The contributor reports bothersome appearance · male subject, age 70–79 · the top or side of the foot and leg are involved · the contributor reports the lesion is raised or bumpy · a close-up photograph:
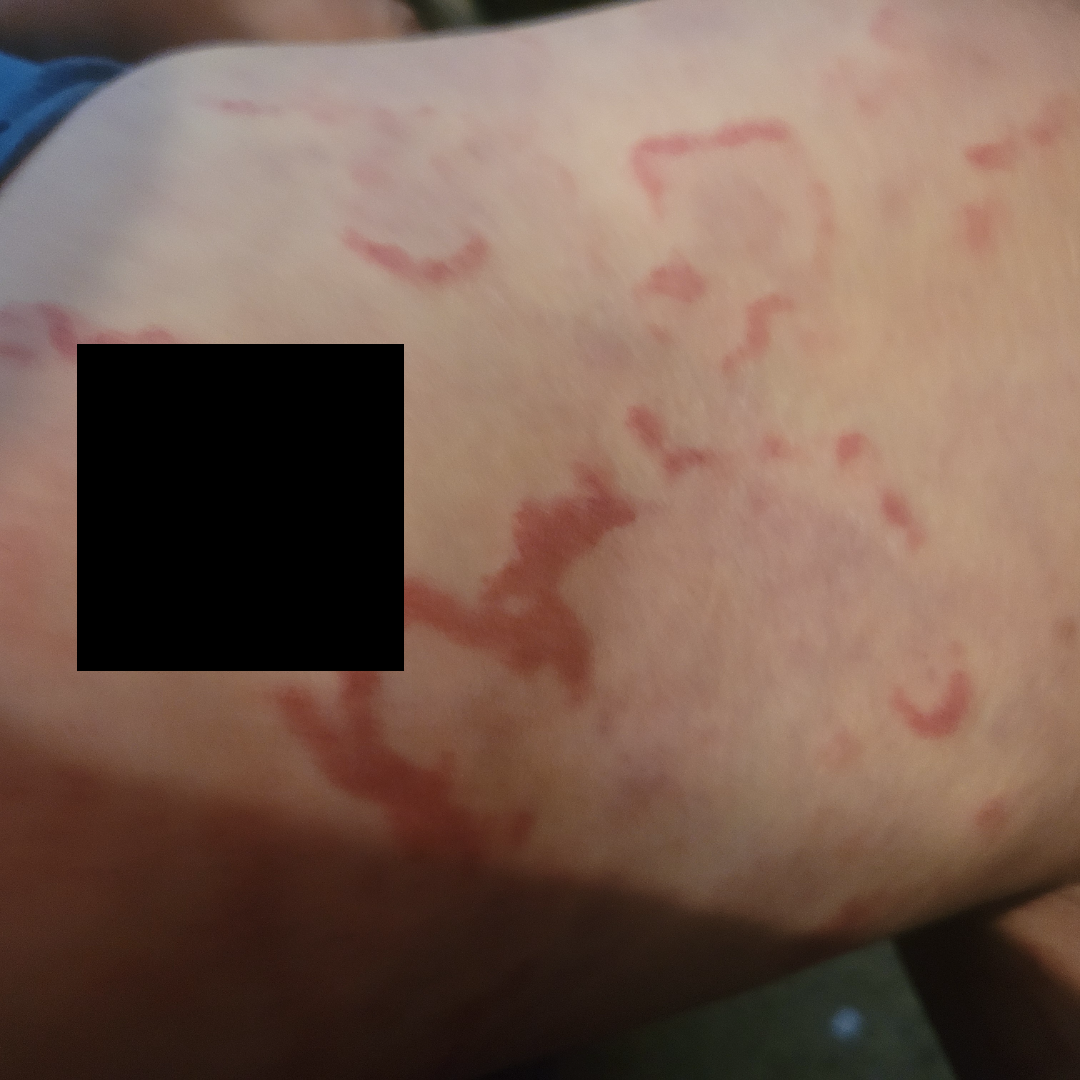Findings: Erythema gyratum repens (most likely); Drug Rash (possible).